The patient is male · this image was taken at an angle:
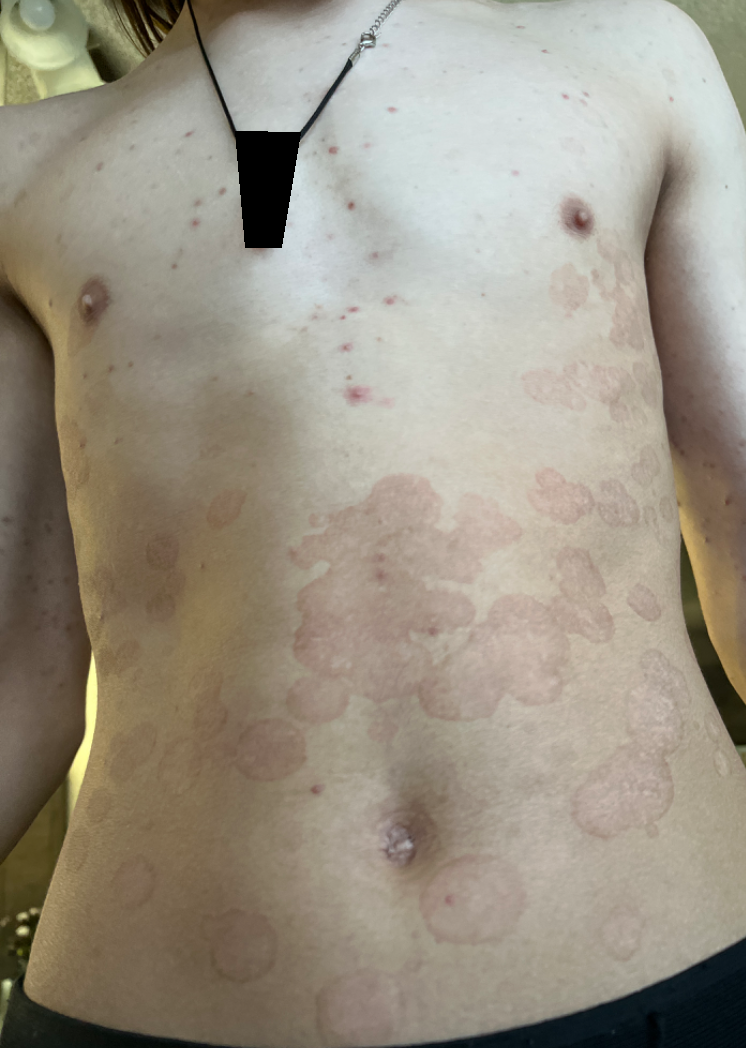Favoring Psoriasis.